Recorded as Fitzpatrick phototype III · a smartphone photograph of a skin lesion · the chart notes pesticide exposure and no prior malignancy (patient or family) · a female subject 85 years old: 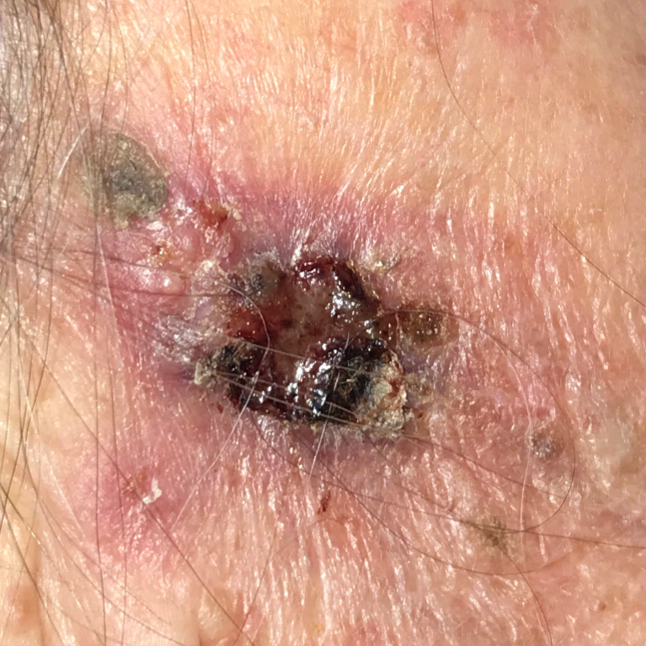The lesion is located on an ear.
The lesion measures 35 × 25 mm.
By the patient's account, the lesion has grown, is elevated, has bled, and has changed.
Biopsy-confirmed as a basal cell carcinoma.